Located on the leg, the photograph was taken at a distance:
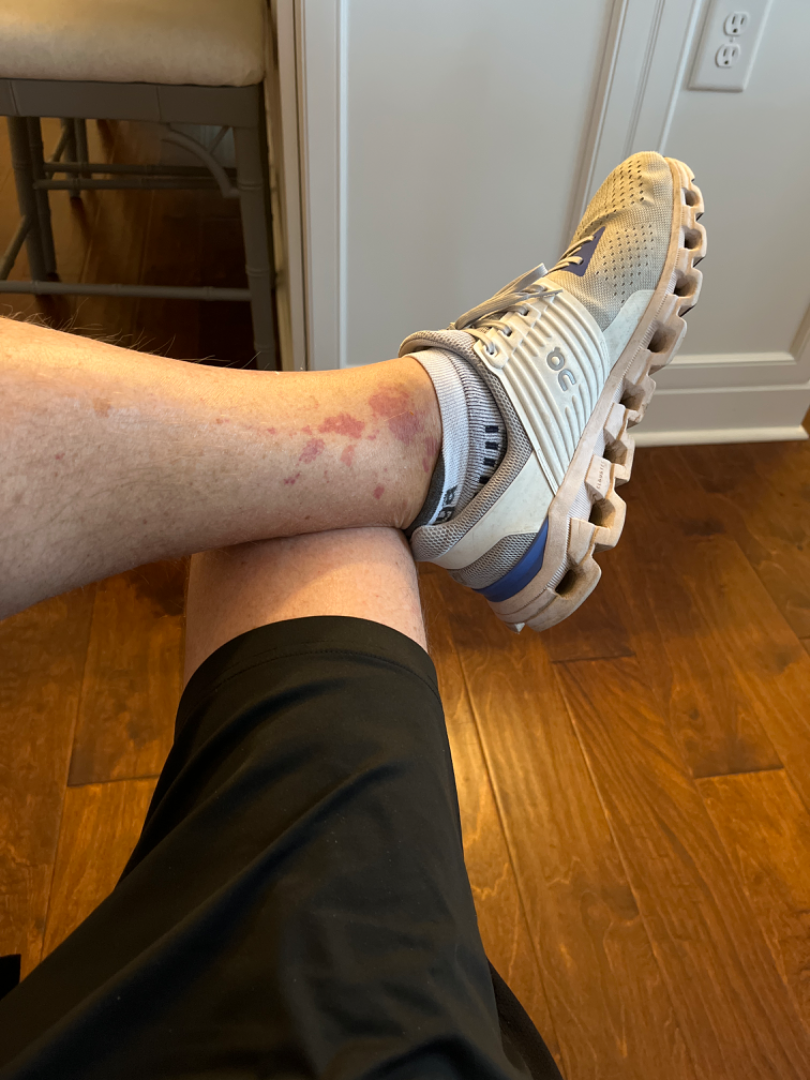Impression:
The case was indeterminate on photographic review.
History:
Present for less than one week. The patient did not report lesion symptoms. Self-categorized by the patient as a rash. Texture is reported as flat. Fitzpatrick skin type III.